The lesion involves the arm · the photo was captured at an angle: 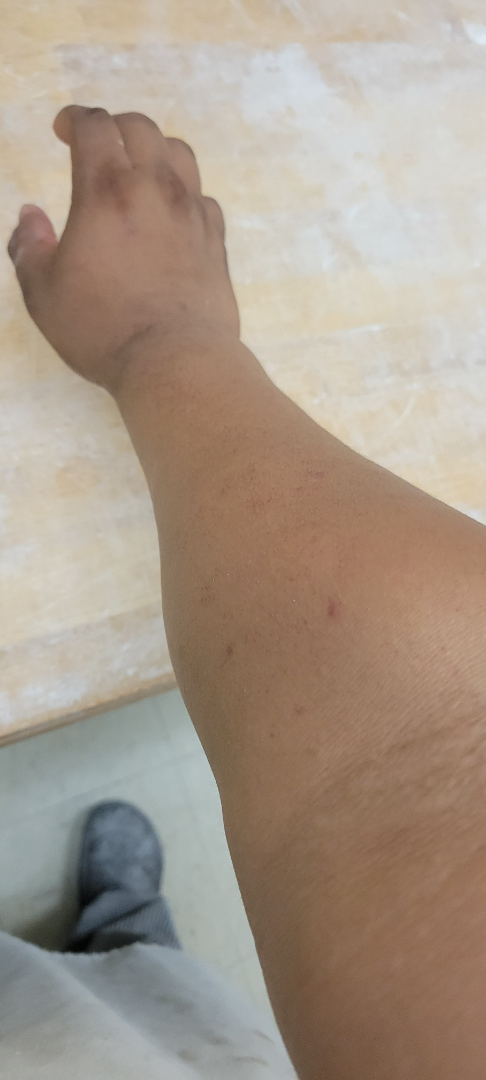Impression: One reviewing dermatologist: Pigmented purpuric eruption and Leukocytoclastic Vasculitis were considered with similar weight.